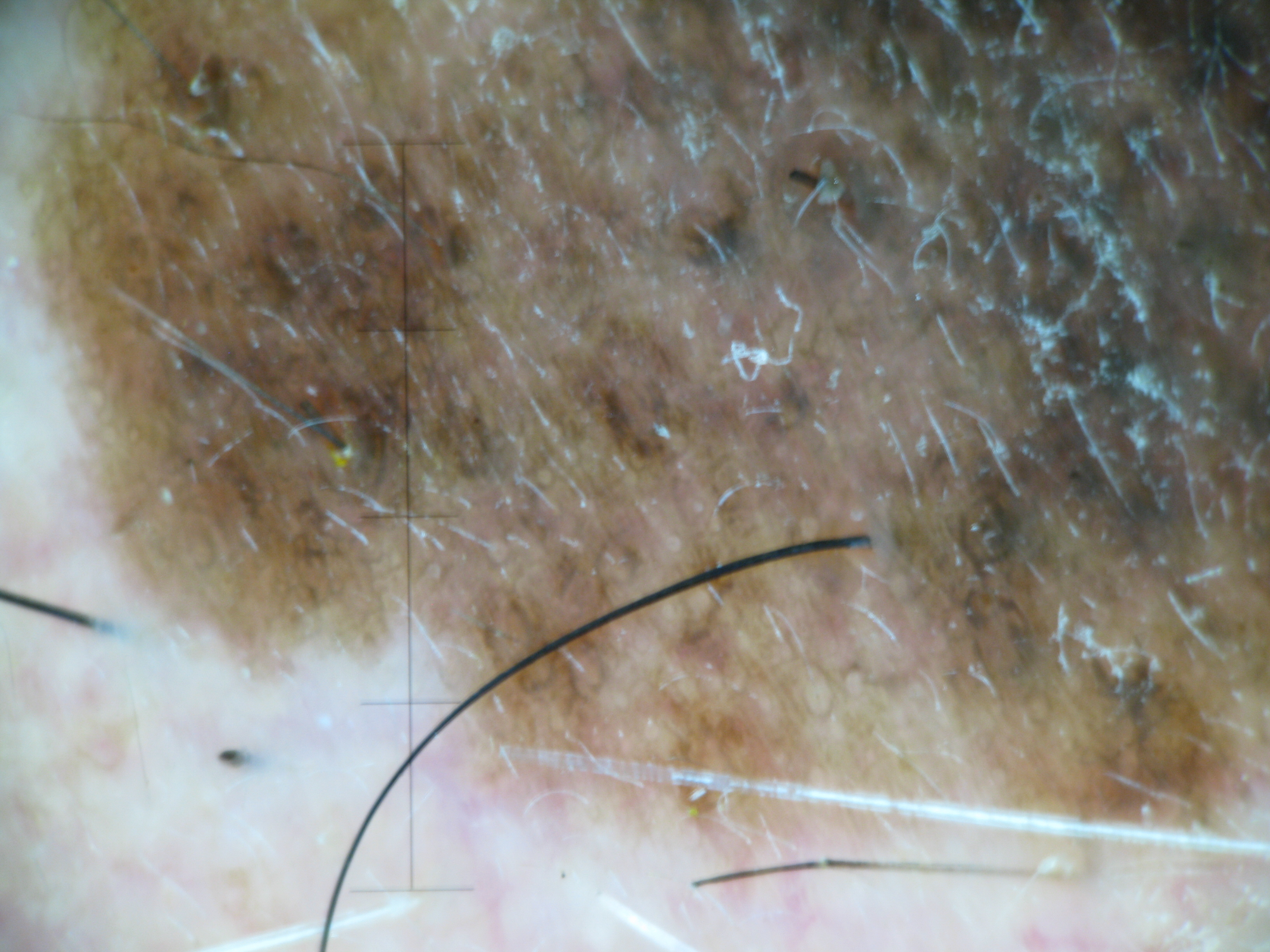Confirmed on histopathology as a lentigo maligna.